Imaged for a research study, with no referral diagnosis recorded; a dermoscopy image of a skin lesion; a female subject 78 years old.
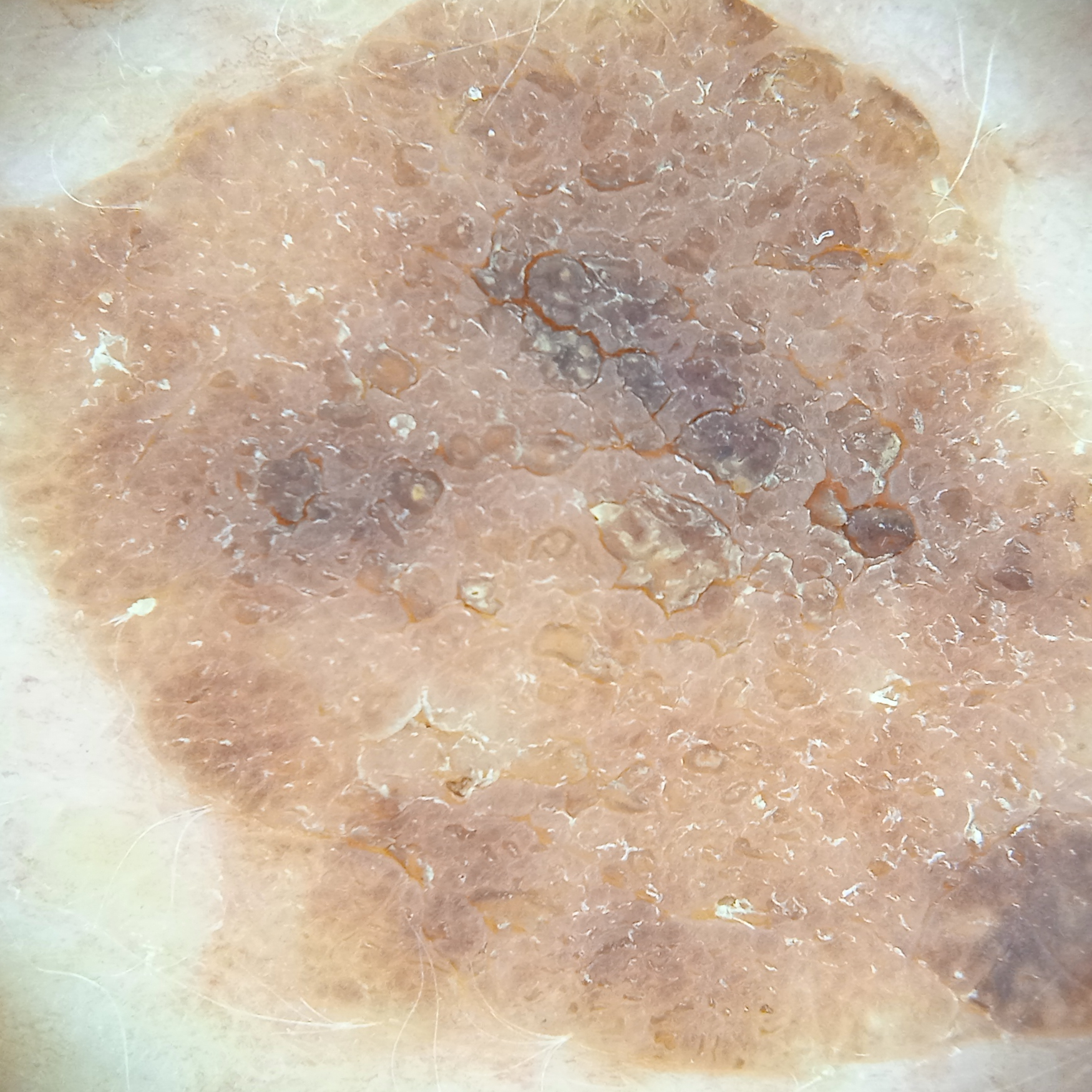Located on the back. Measuring roughly 15.7 mm. The diagnostic impression was a seborrheic keratosis.